The subject is a male roughly 60 years of age. A skin lesion imaged with a dermatoscope — 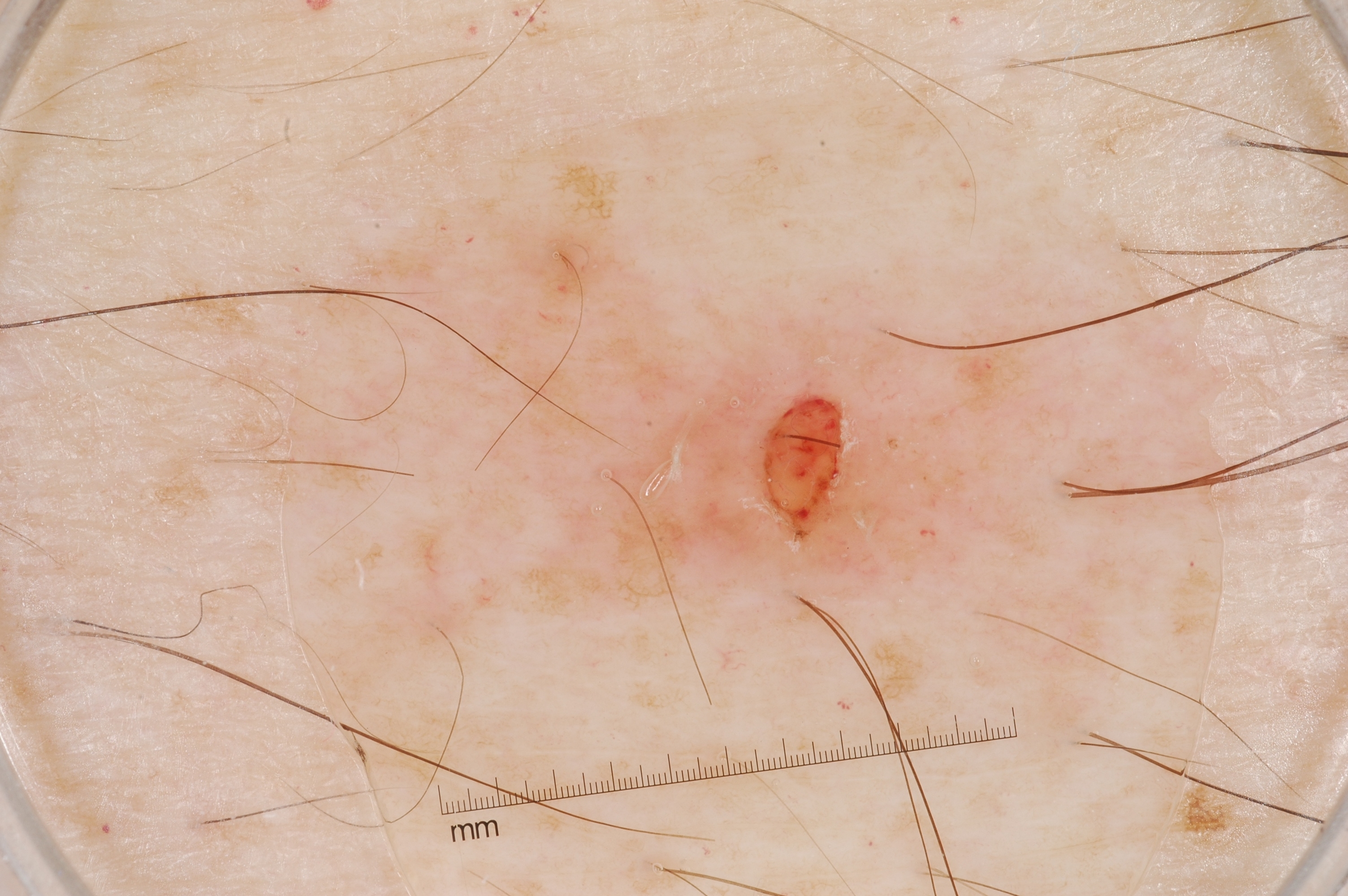– dermoscopic findings · milia-like cysts; absent: streaks, pigment network, and negative network
– extent · moderate
– lesion bbox · 491 291 1077 602
– diagnosis · a melanocytic nevus